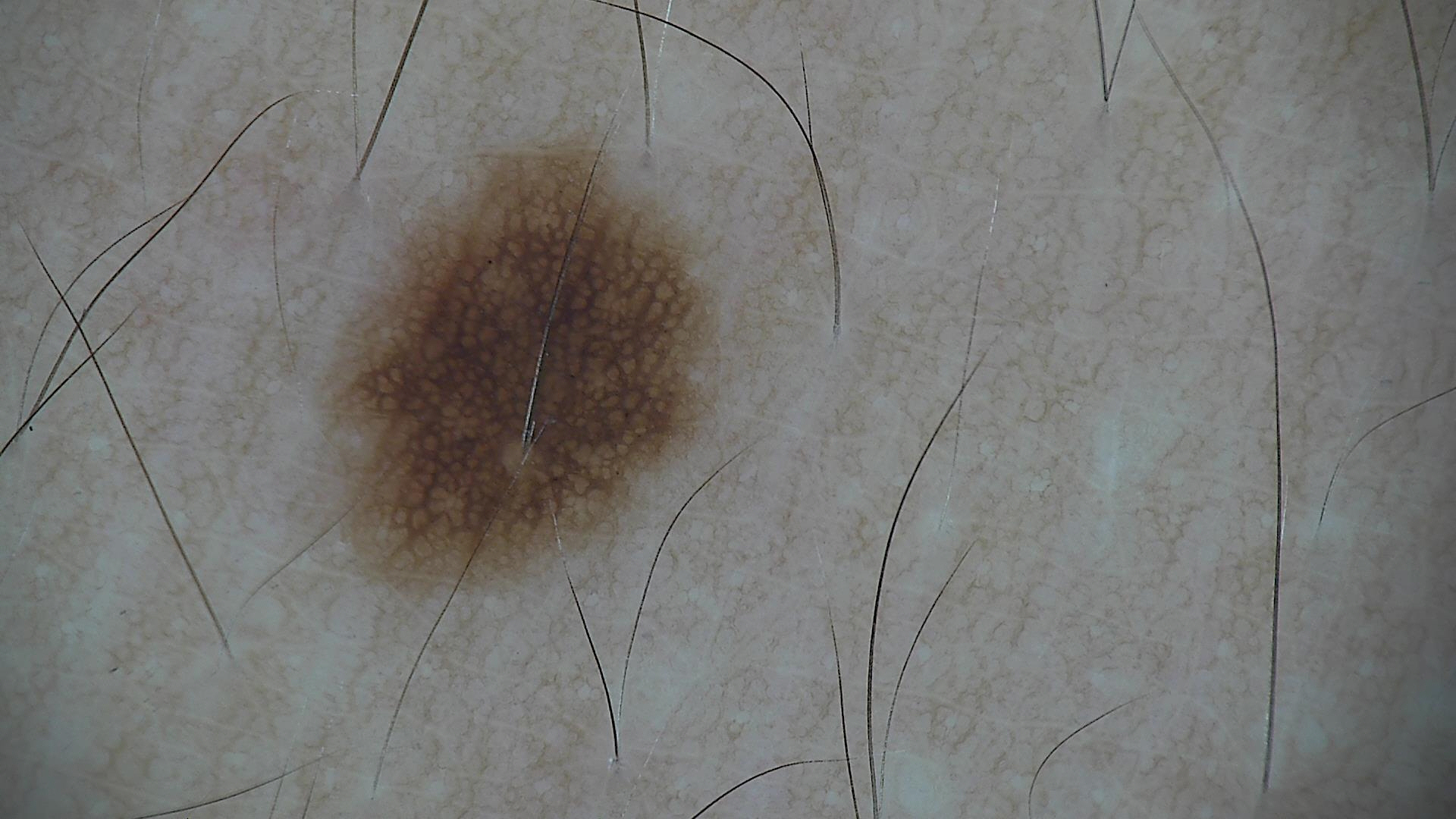Consistent with a dysplastic junctional nevus.